A clinical photograph of a skin lesion. Referred for assessment of suspected basal cell carcinoma. The patient says their skin reddens painfully with sun exposure. A female patient aged 48. On a questionnaire the patient reported a family history of skin cancer, a history of sunbed use, no personal history of cancer, and no immunosuppression. The patient describes having few moles overall:
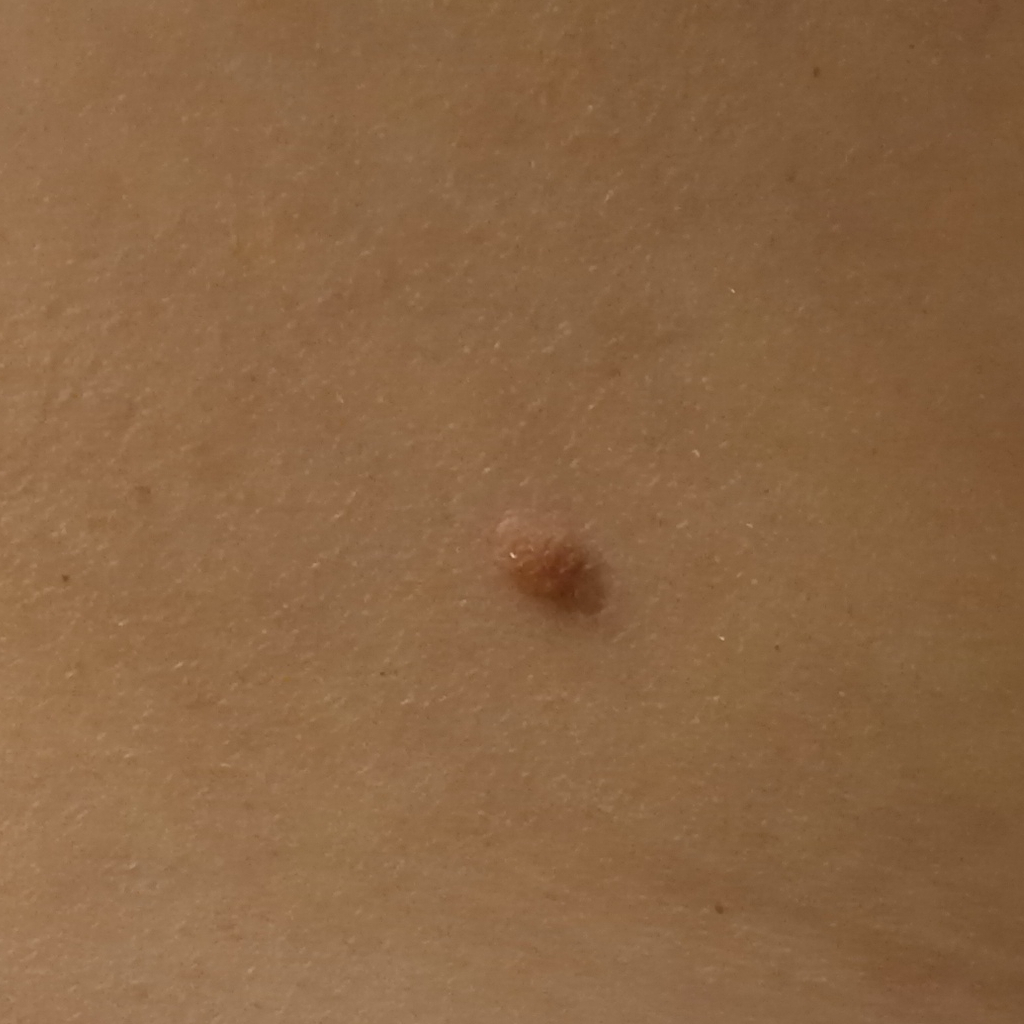size: 12.3 mm | pathology: basal cell carcinoma (biopsy-proven).